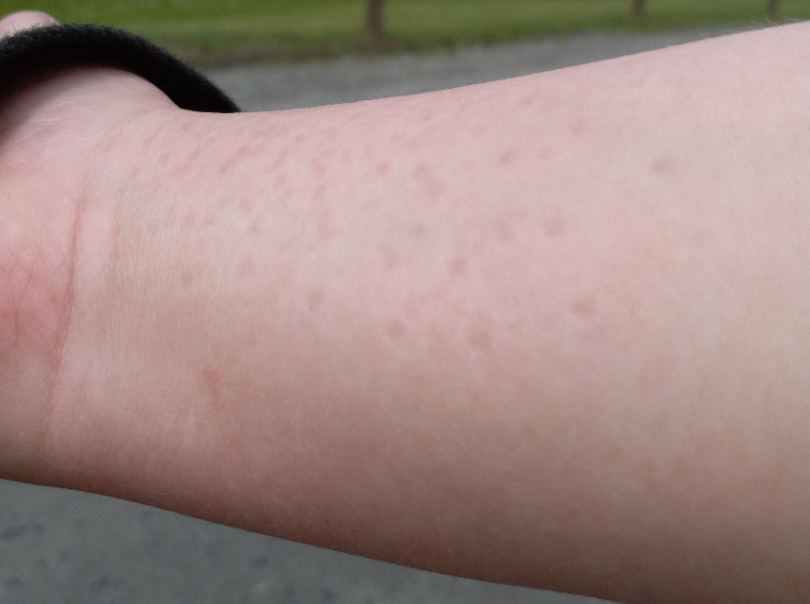Review:
The image was not sufficient for the reviewer to characterize the skin condition.
Patient information:
The photo was captured at an angle.